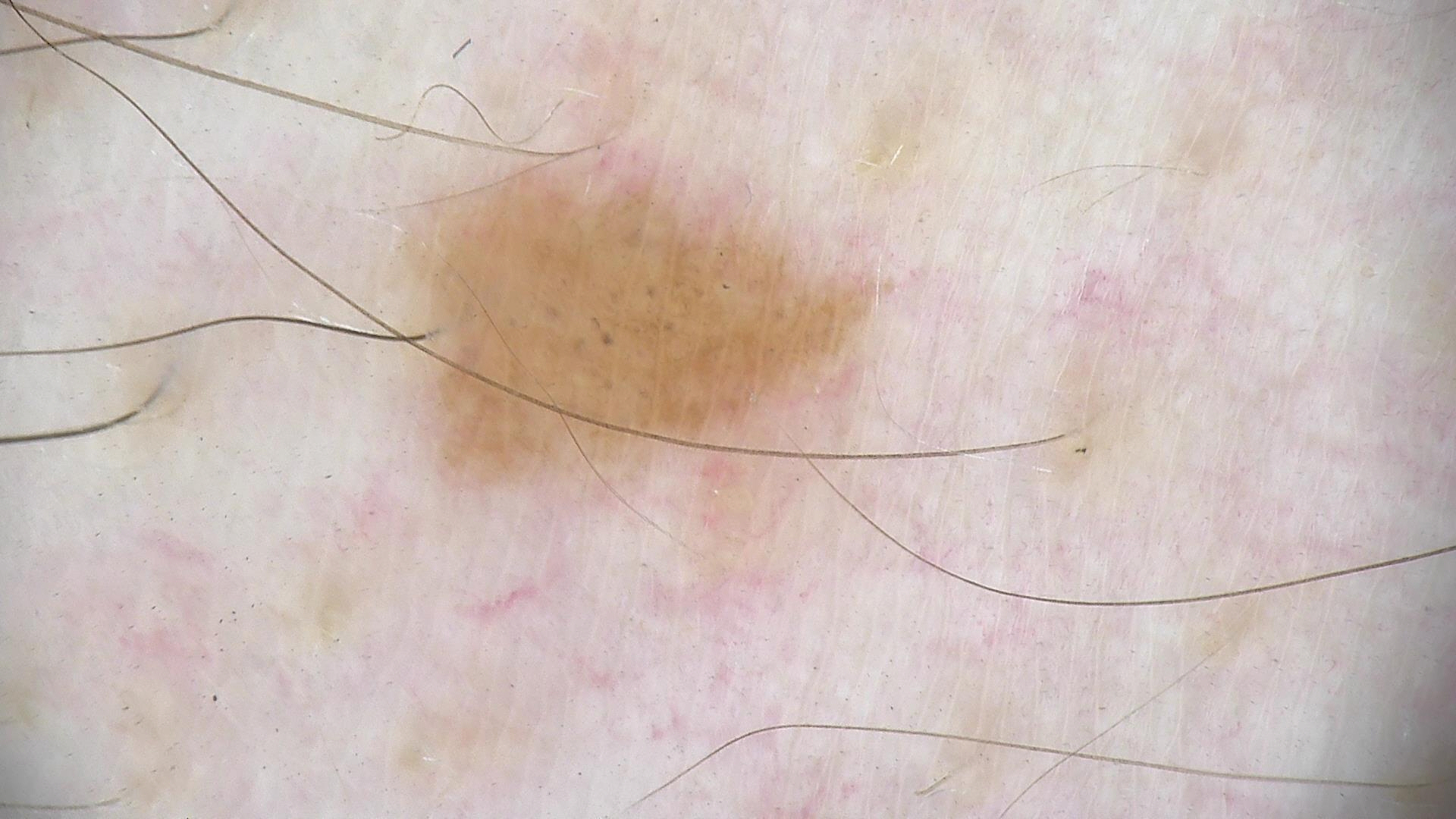{"diagnosis": {"name": "dysplastic junctional nevus", "code": "jd", "malignancy": "benign", "super_class": "melanocytic", "confirmation": "expert consensus"}}